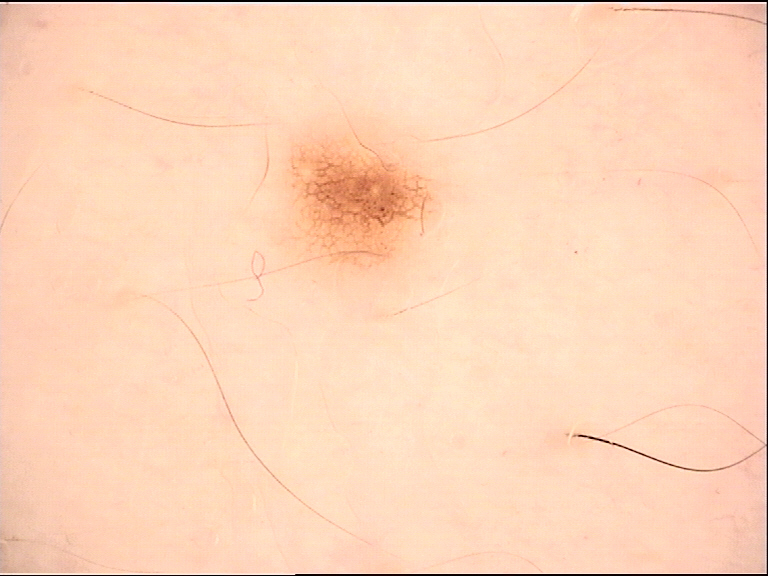label — dysplastic junctional nevus (expert consensus).